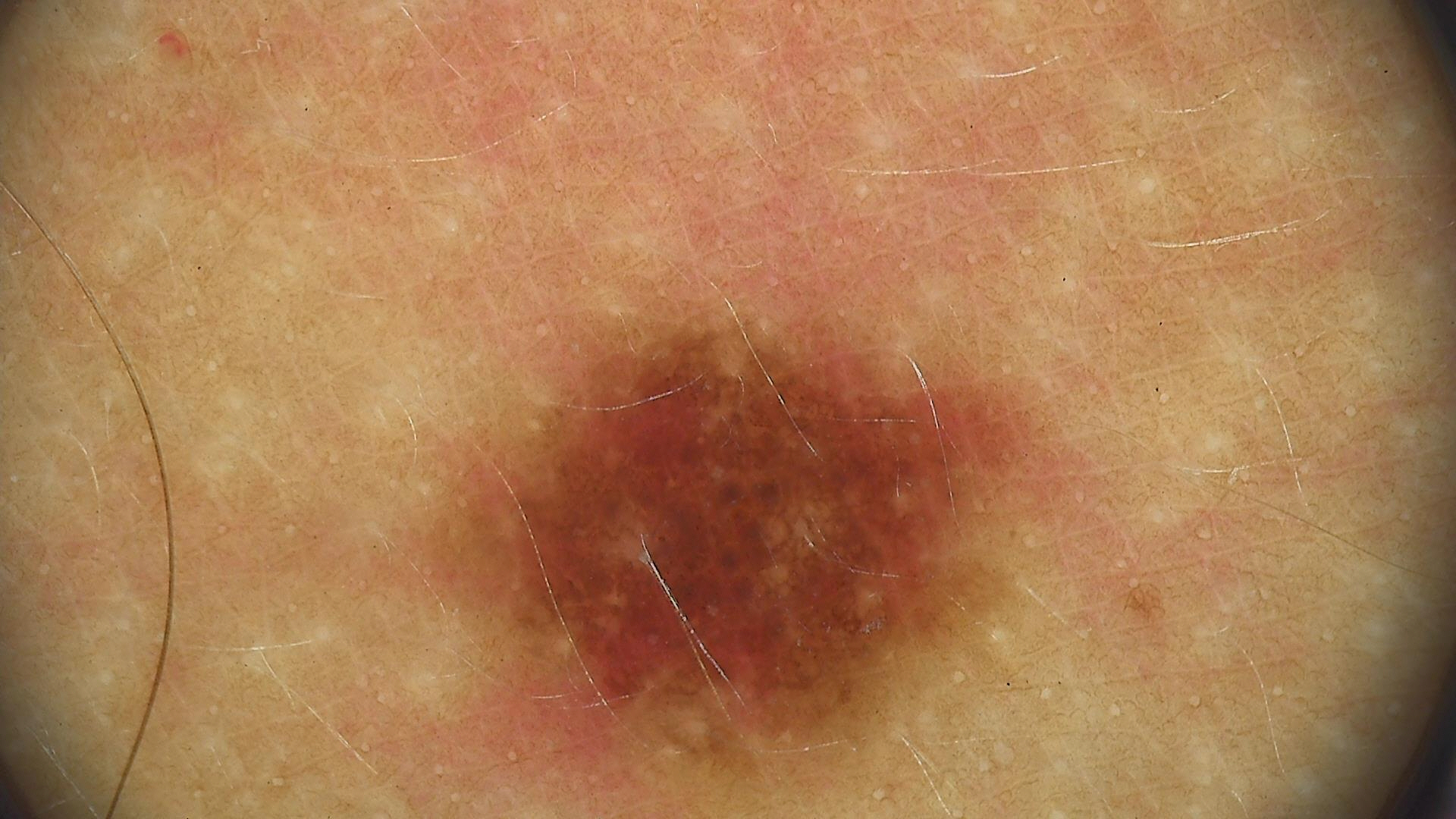Diagnosed as a dysplastic compound nevus.